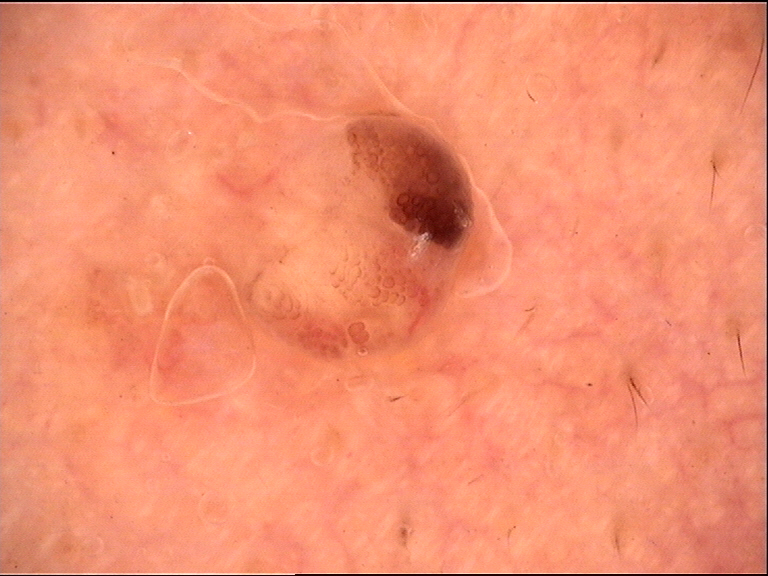A dermoscopic photograph of a skin lesion. The morphology is that of a banal lesion. The diagnosis was a dermal nevus.